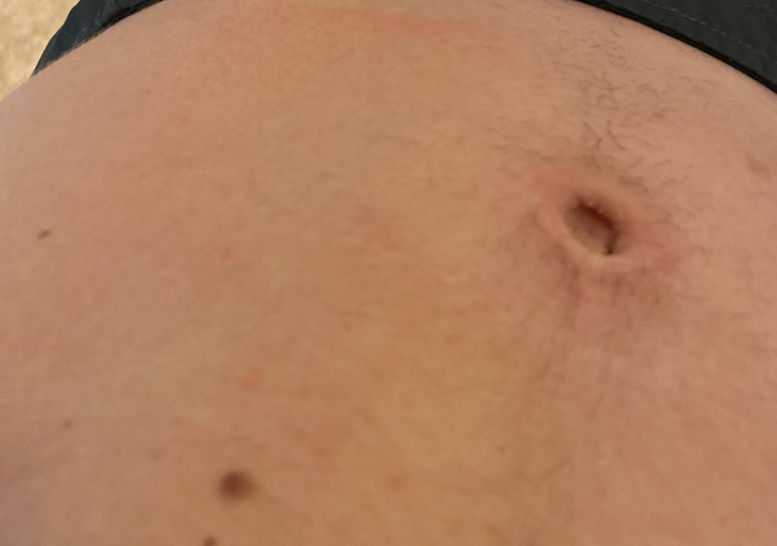differential — Acute and chronic dermatitis (100%)